A dermoscopy image of a single skin lesion.
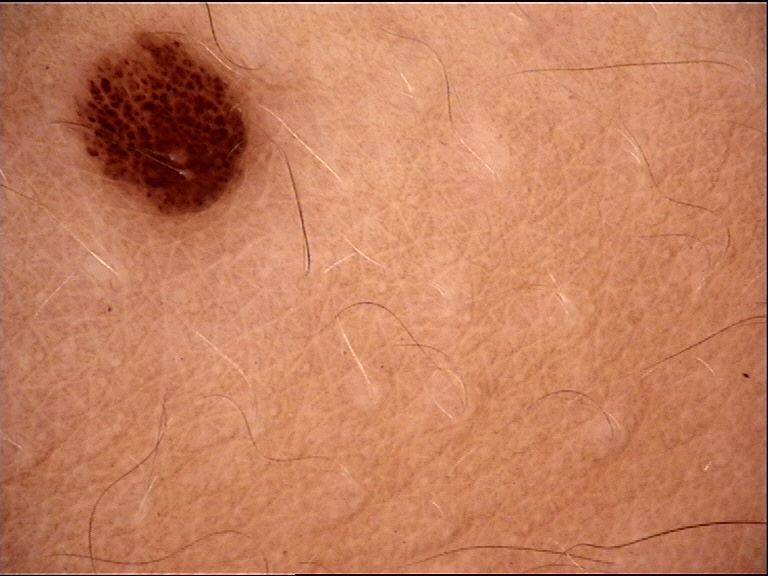<case>
<diagnosis>
<name>junctional nevus</name>
<code>jb</code>
<malignancy>benign</malignancy>
<super_class>melanocytic</super_class>
<confirmation>expert consensus</confirmation>
</diagnosis>
</case>